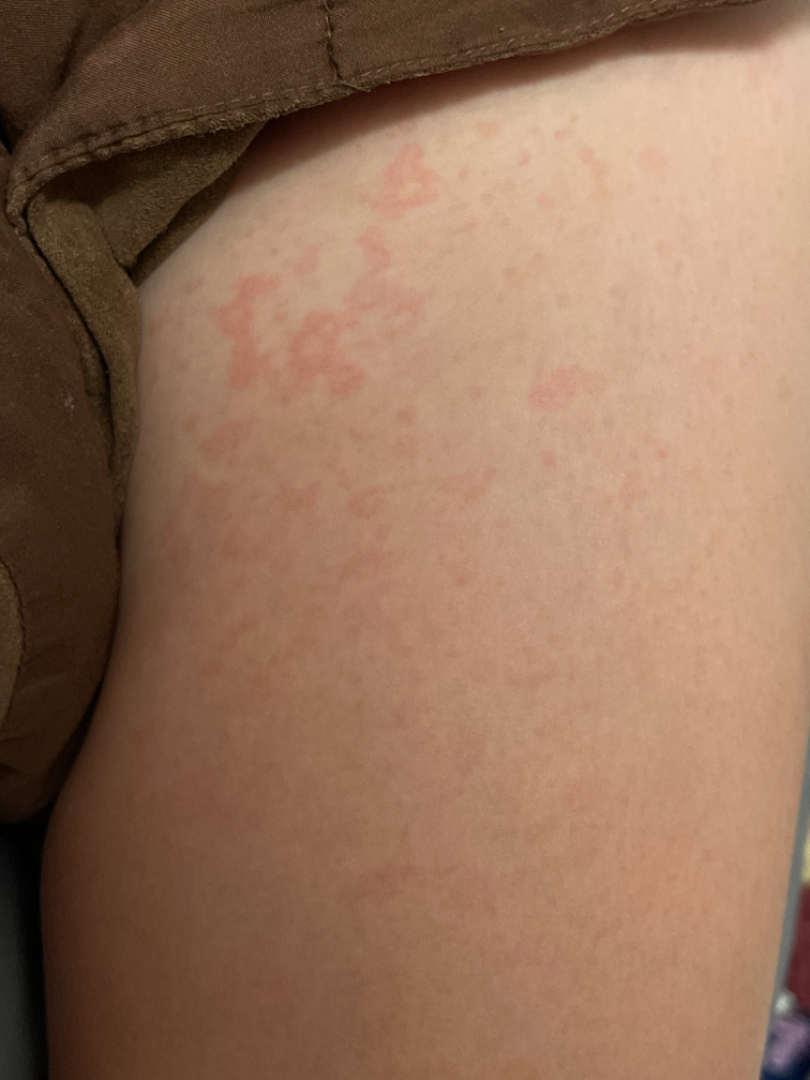Q: Image view?
A: at a distance
Q: Anatomic location?
A: front of the torso, arm, back of the hand and leg
Q: What conditions are considered?
A: Drug Rash and Viral Exanthem were considered with similar weight